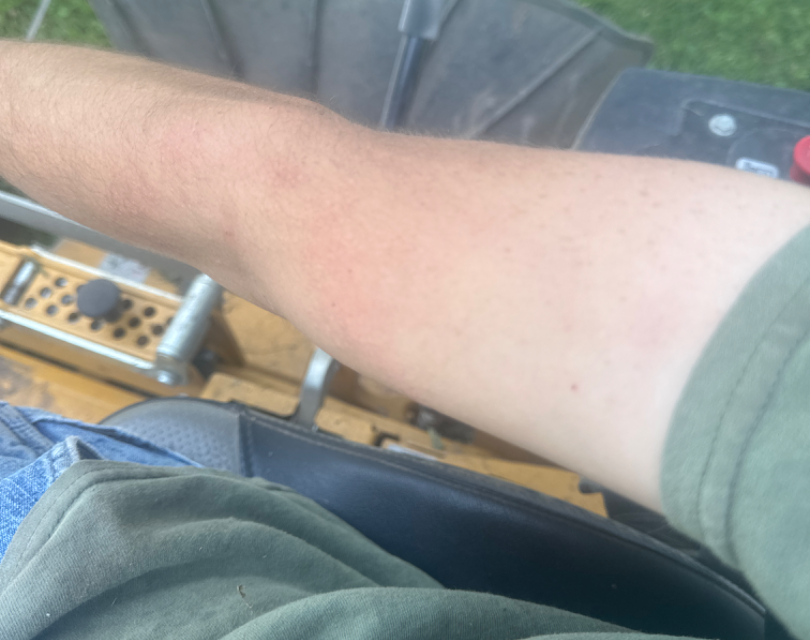| key | value |
|---|---|
| described texture | rough or flaky |
| patient describes the issue as | a rash |
| body site | arm |
| shot type | at a distance |
| duration | less than one week |
| patient-reported symptoms | enlargement and itching |
| impression | the differential is split between Eczema, Allergic Contact Dermatitis and Irritant Contact Dermatitis |